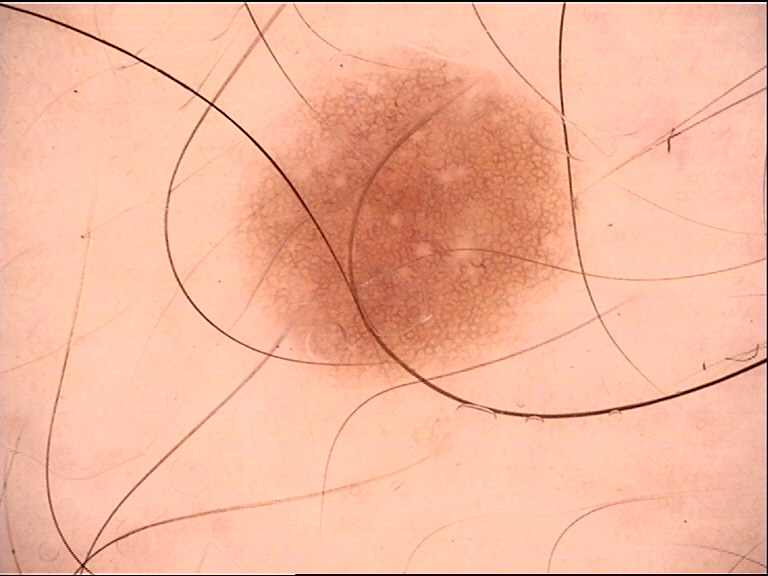{"image": "dermoscopy", "diagnosis": {"name": "dysplastic junctional nevus", "code": "jd", "malignancy": "benign", "super_class": "melanocytic", "confirmation": "expert consensus"}}